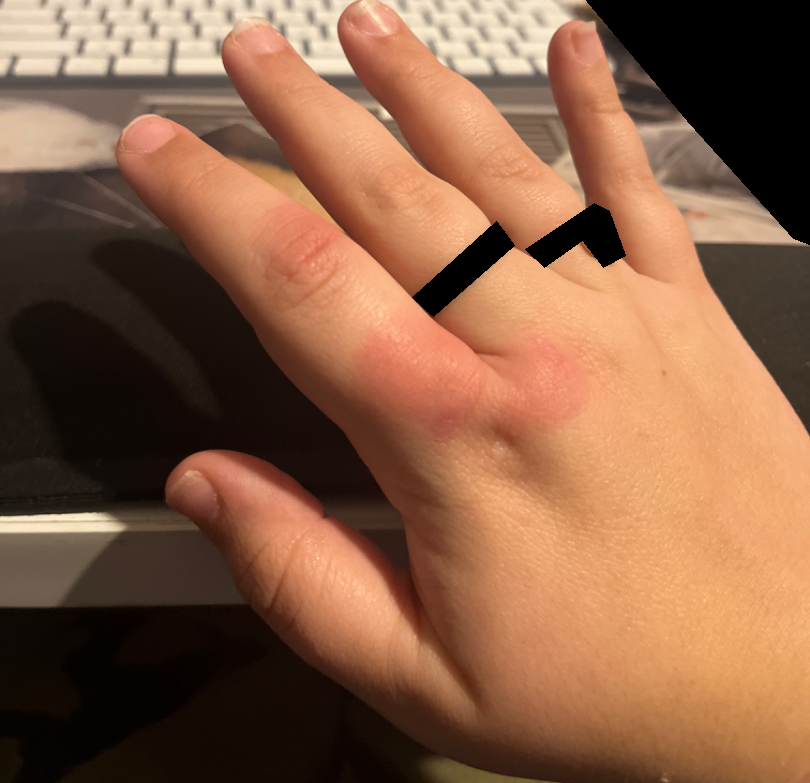view = close-up
subject = female, age 18–29
body site = back of the hand
clinical impression = Urticaria (considered); Insect Bite (considered); Cellulitis (less likely)